The photograph is a close-up of the affected area: 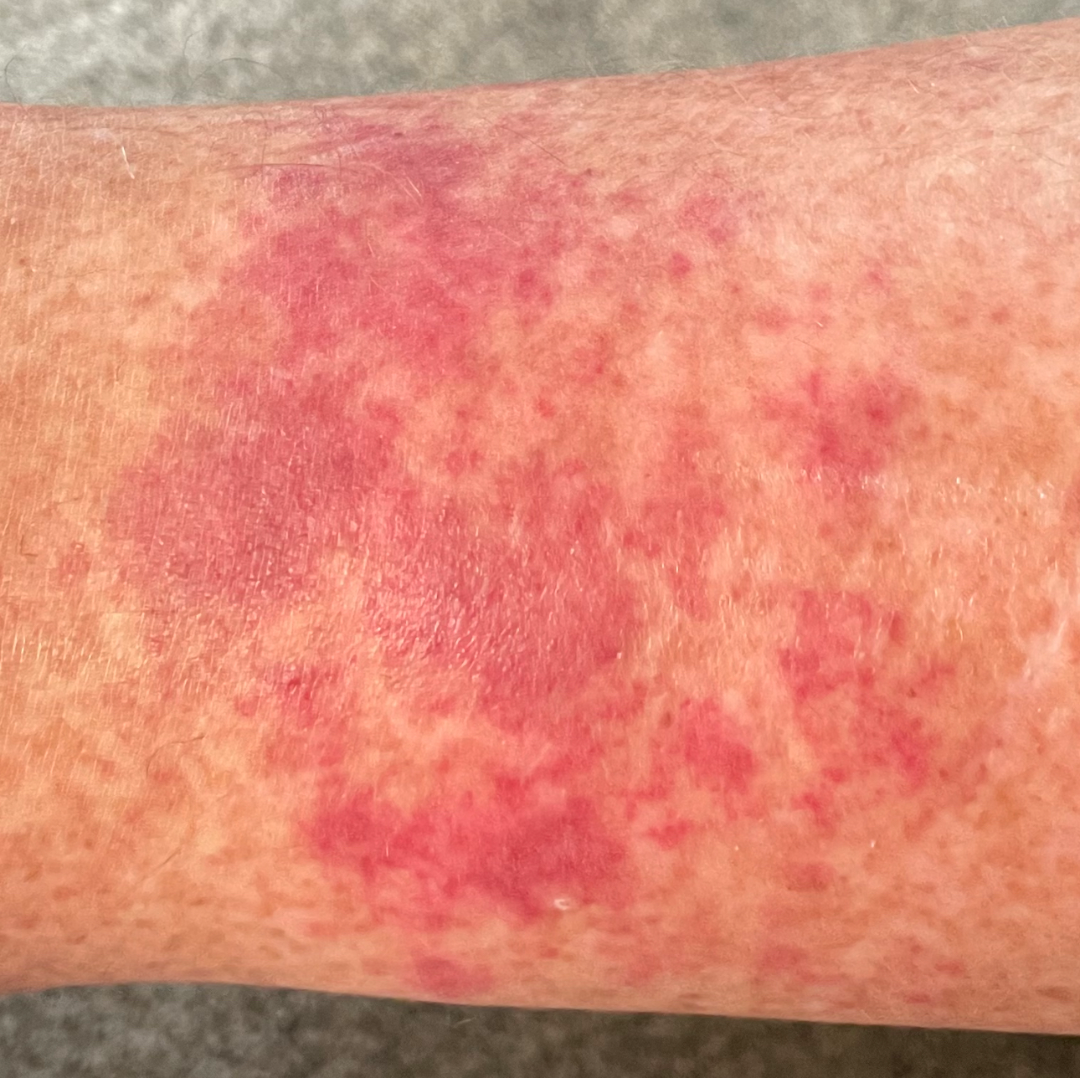assessment=indeterminate